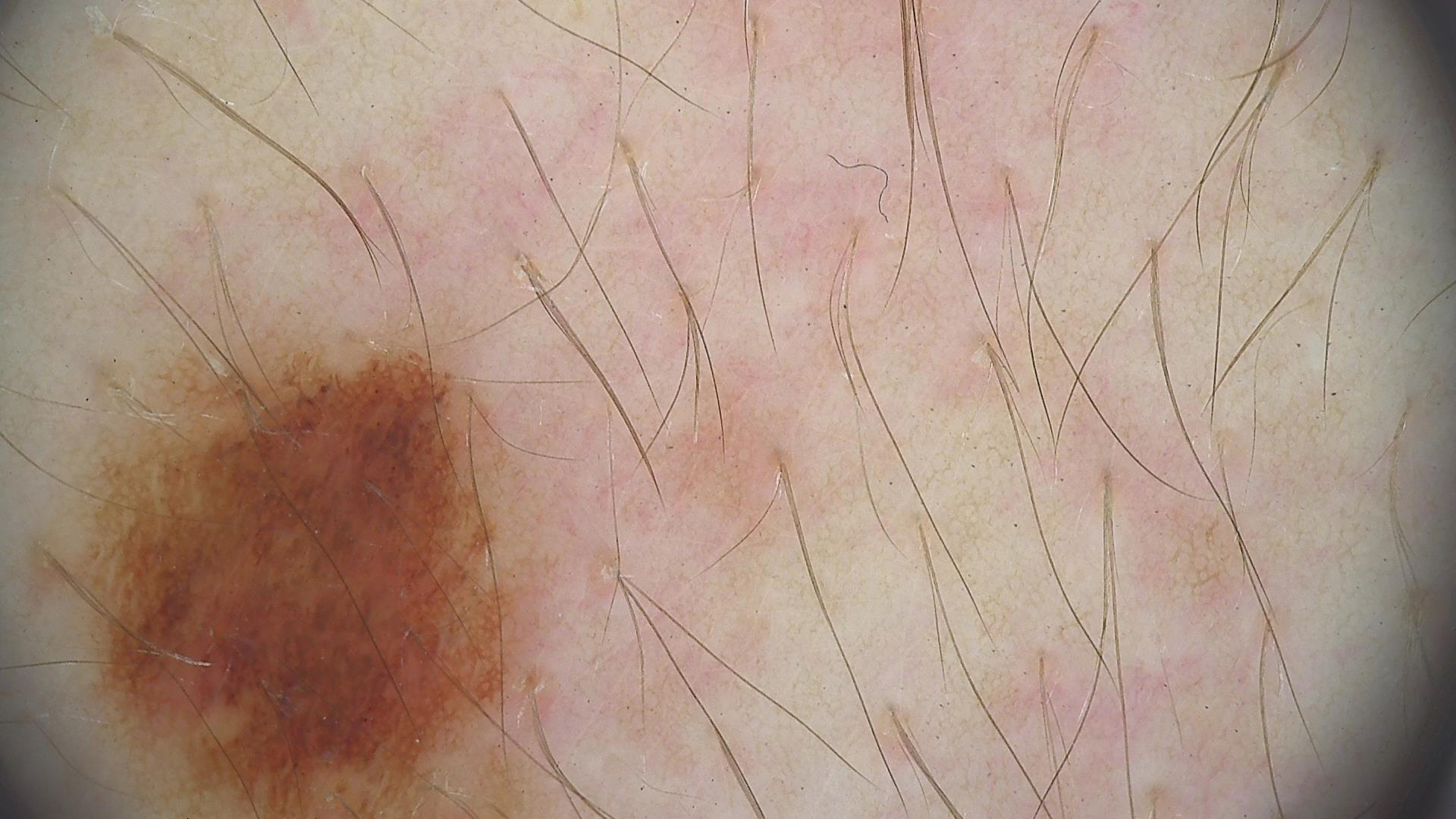Labeled as a dysplastic junctional nevus.